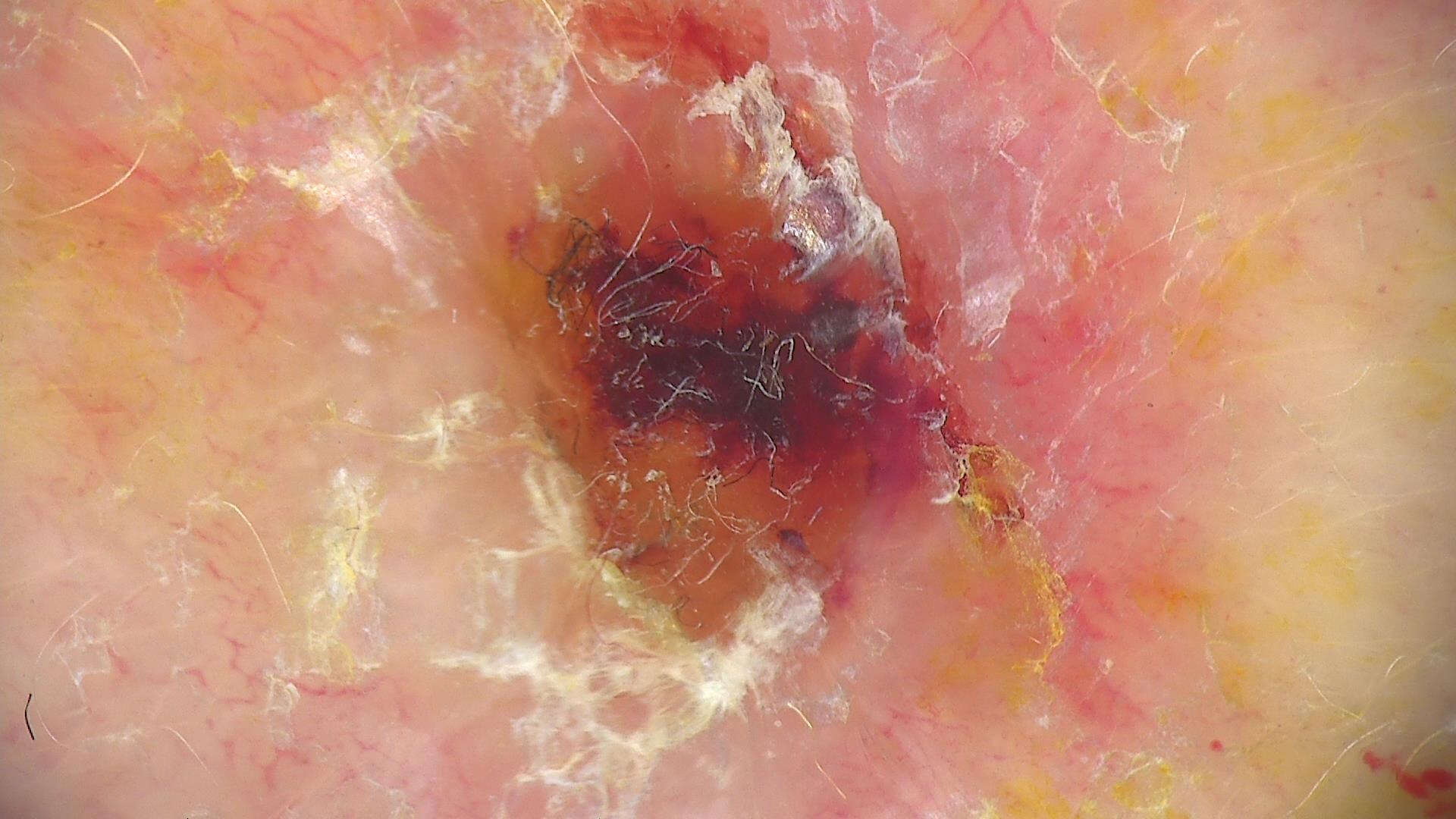| field | value |
|---|---|
| lesion type | keratinocytic |
| pathology | squamous cell carcinoma (biopsy-proven) |